A skin lesion imaged with a dermatoscope — 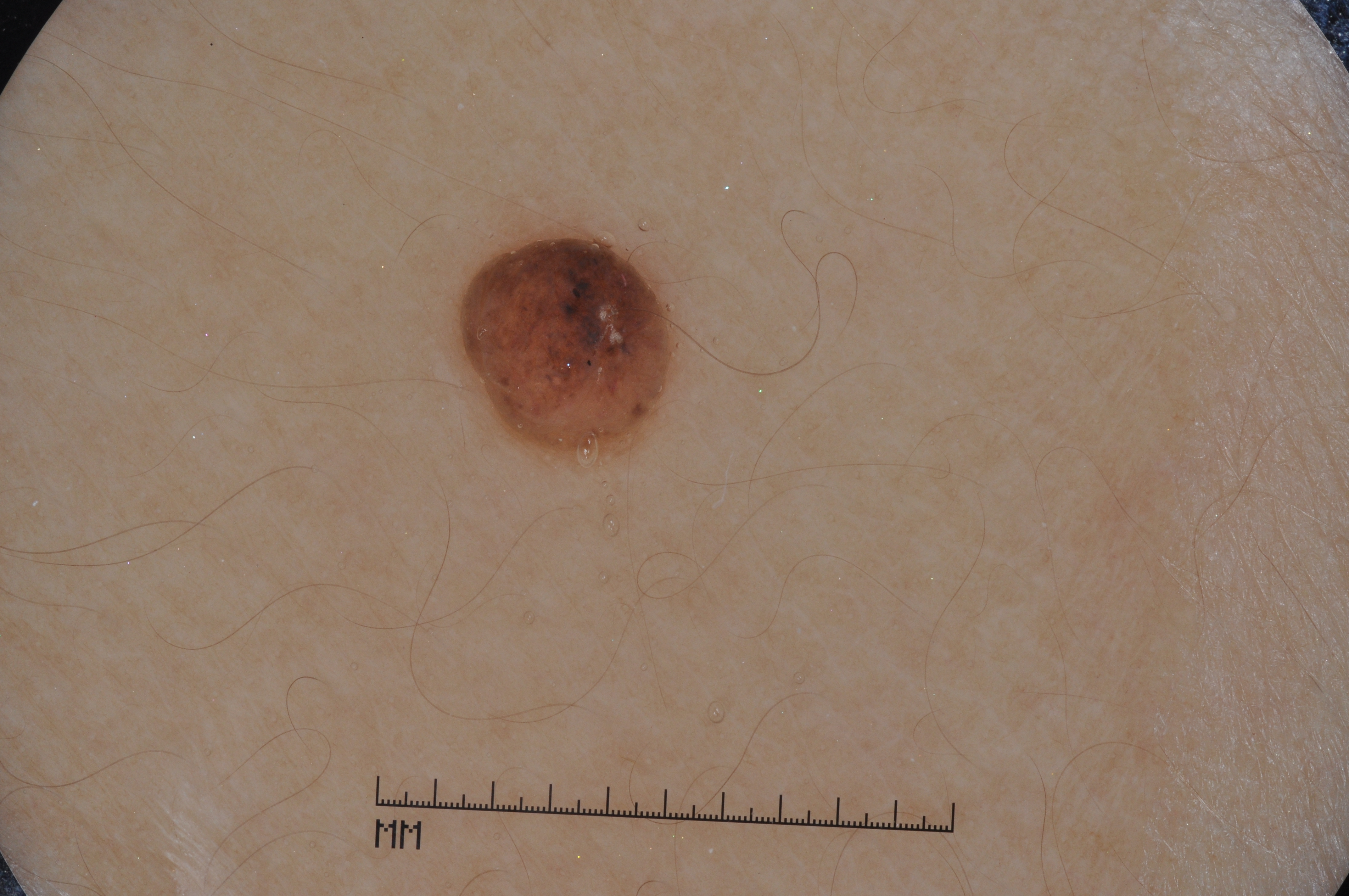Q: Which dermoscopic features are absent?
A: milia-like cysts, pigment network, streaks, and negative network
Q: How large is the lesion within the image?
A: small
Q: Where is the lesion in the image?
A: <box>453, 222, 714, 461</box>
Q: What did the assessment conclude?
A: a melanocytic nevus, a benign lesion